A dermatoscopic image of a skin lesion: 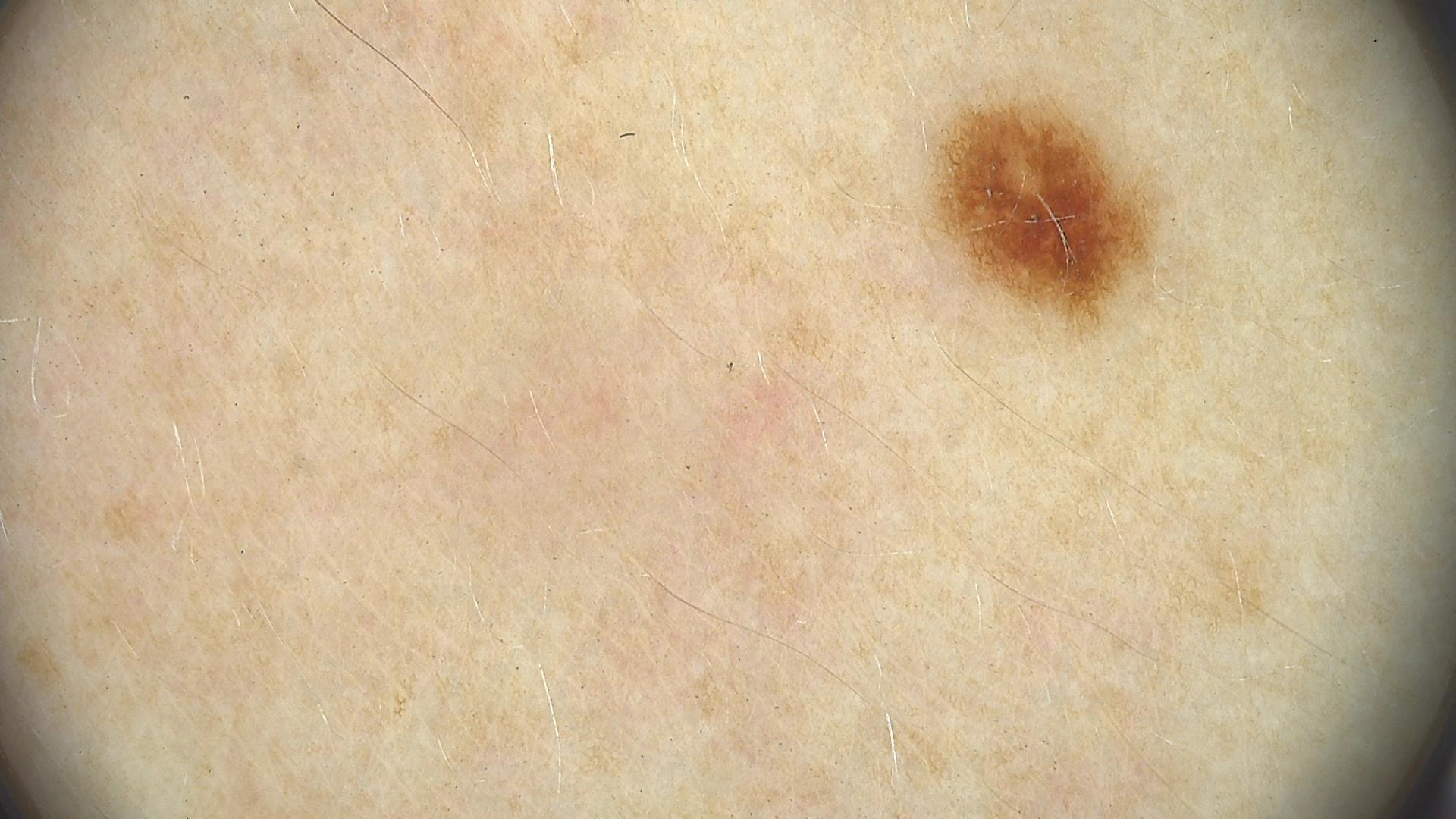{"diagnosis": {"name": "junctional nevus", "code": "jb", "malignancy": "benign", "super_class": "melanocytic", "confirmation": "expert consensus"}}